A dermoscopic image of a skin lesion.
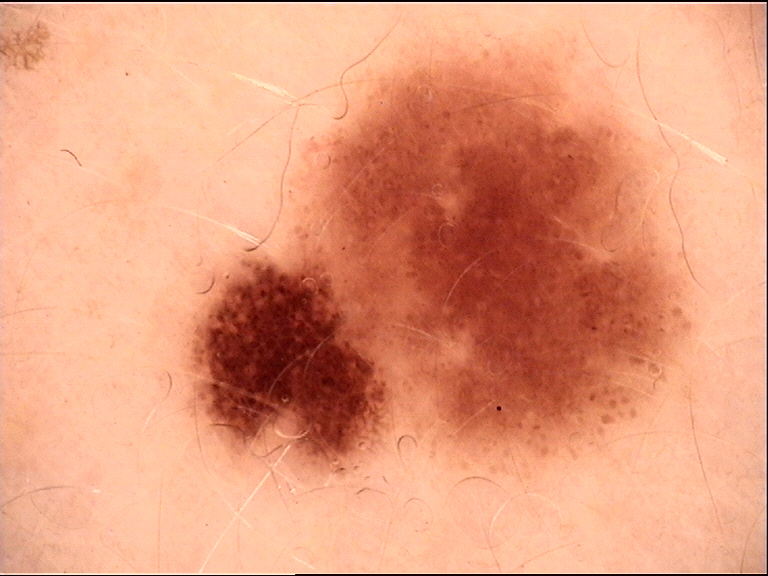Consistent with a dysplastic junctional nevus.